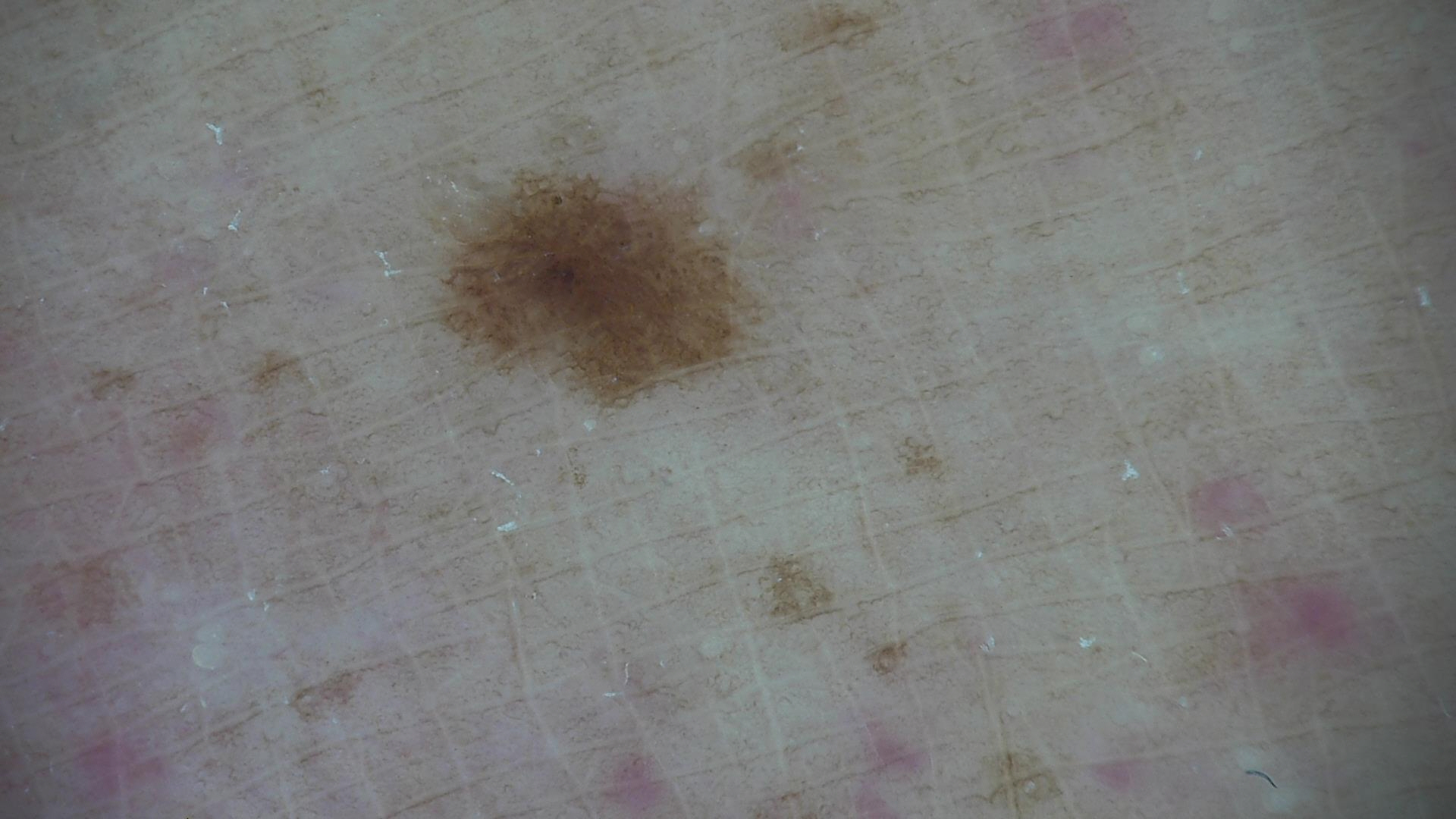Q: What is the imaging modality?
A: dermatoscopy
Q: What is this lesion?
A: dysplastic junctional nevus (expert consensus)